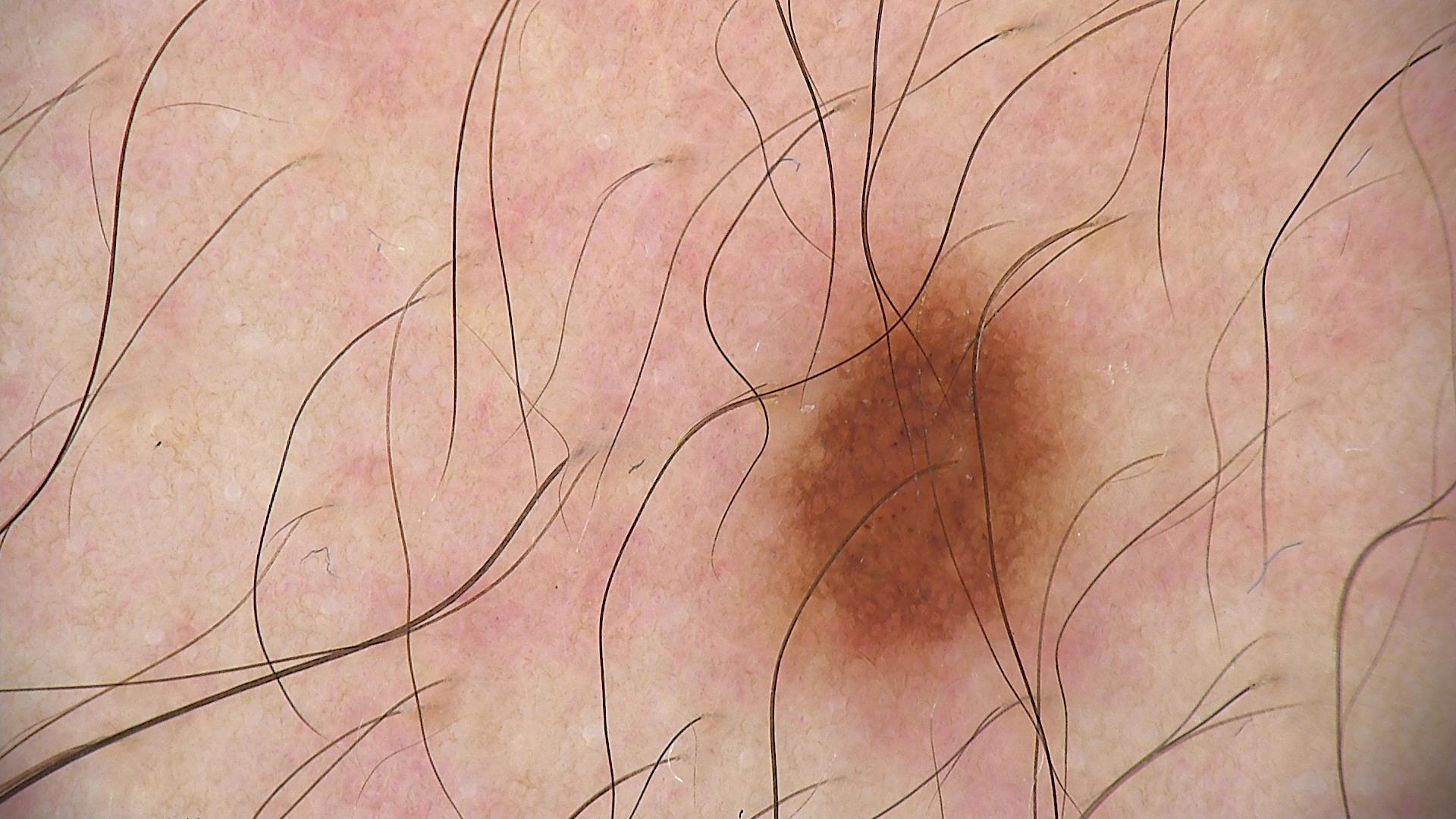| field | value |
|---|---|
| class | dysplastic junctional nevus (expert consensus) |